The affected area is the leg. Female contributor, age 18–29. The photograph is a close-up of the affected area.
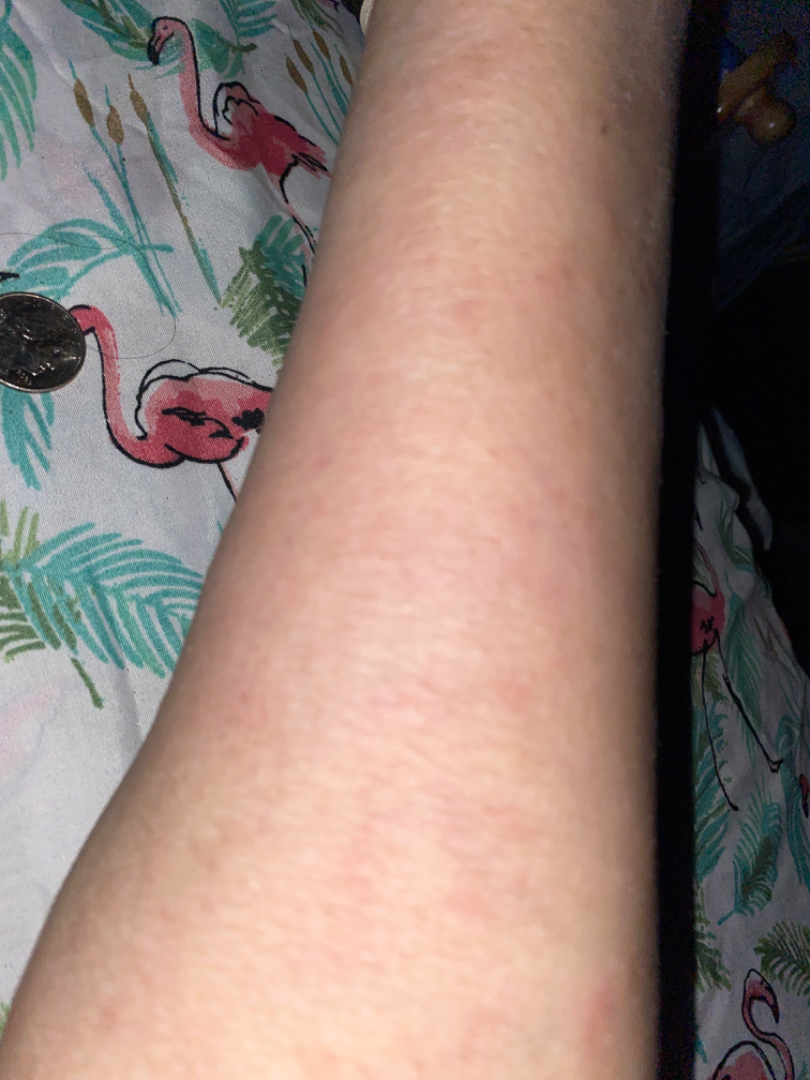assessment = not assessable
lesion symptoms = pain and itching
skin tone = FST III
lesion texture = flat
patient's own categorization = a rash
symptom duration = one to four weeks